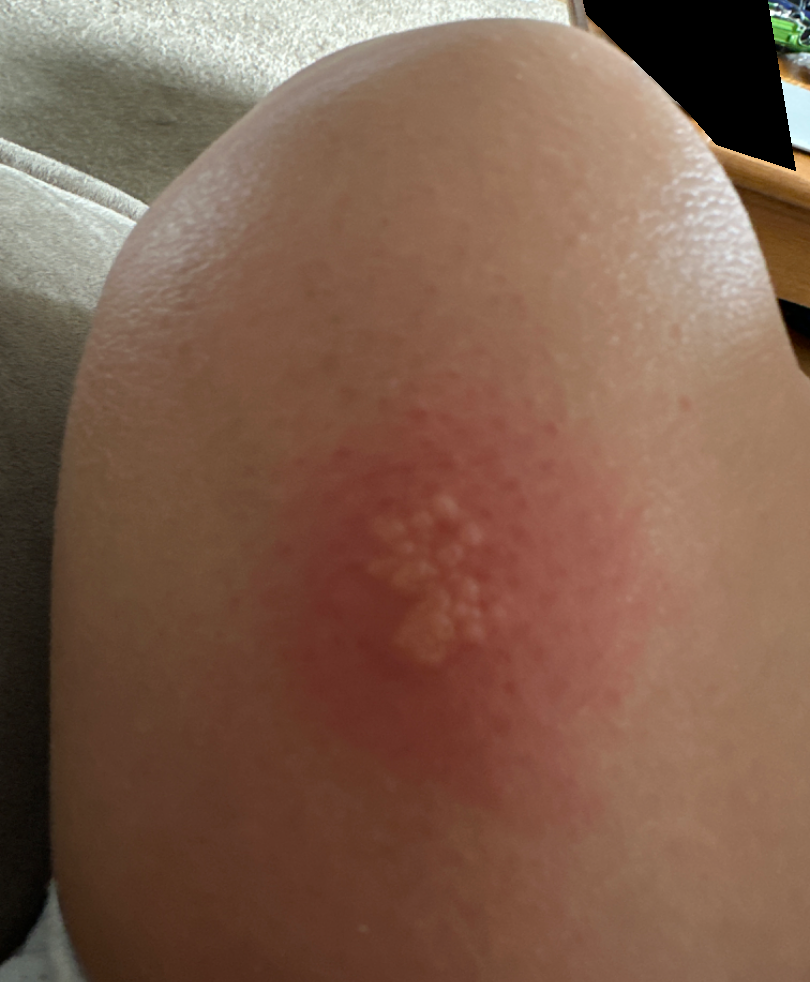  shot_type: close-up
  texture: raised or bumpy
  patient: female, age 18–29
  symptoms:
    - enlargement
    - itching
  duration: more than one year
  body_site: leg
  patient_category: a rash
  differential:
    leading:
      - Herpes Simplex